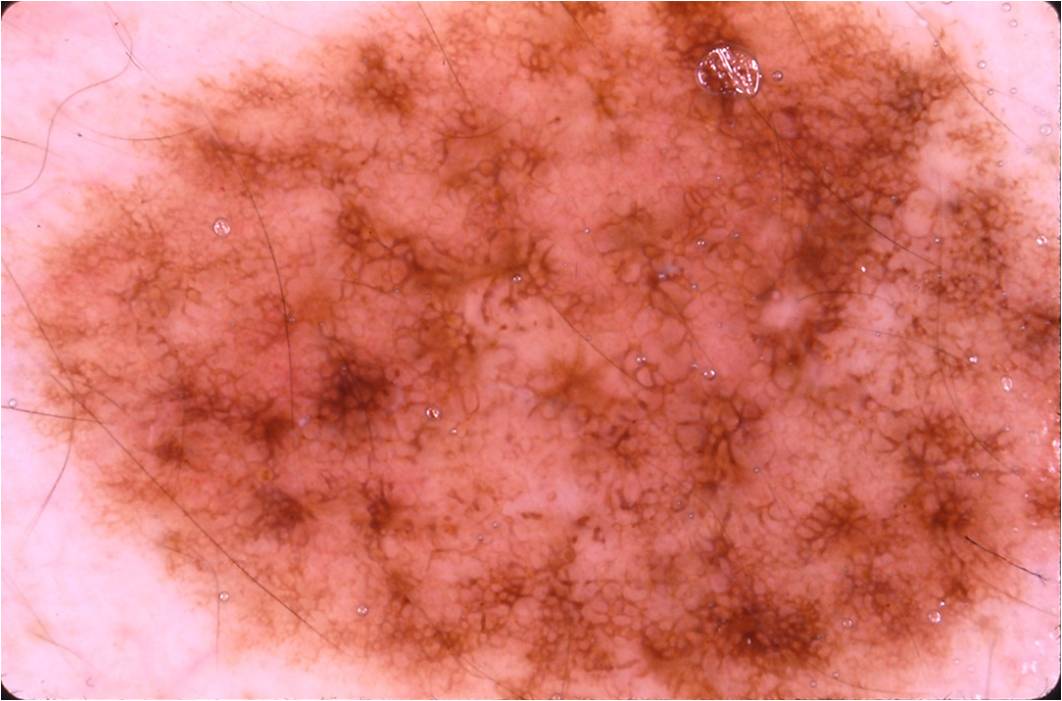Case summary:
This is a dermoscopic photograph of a skin lesion. The lesion stretches across essentially the whole frame.
Conclusion:
The diagnostic assessment was a melanocytic nevus, a benign skin lesion.